A skin lesion imaged with a dermatoscope.
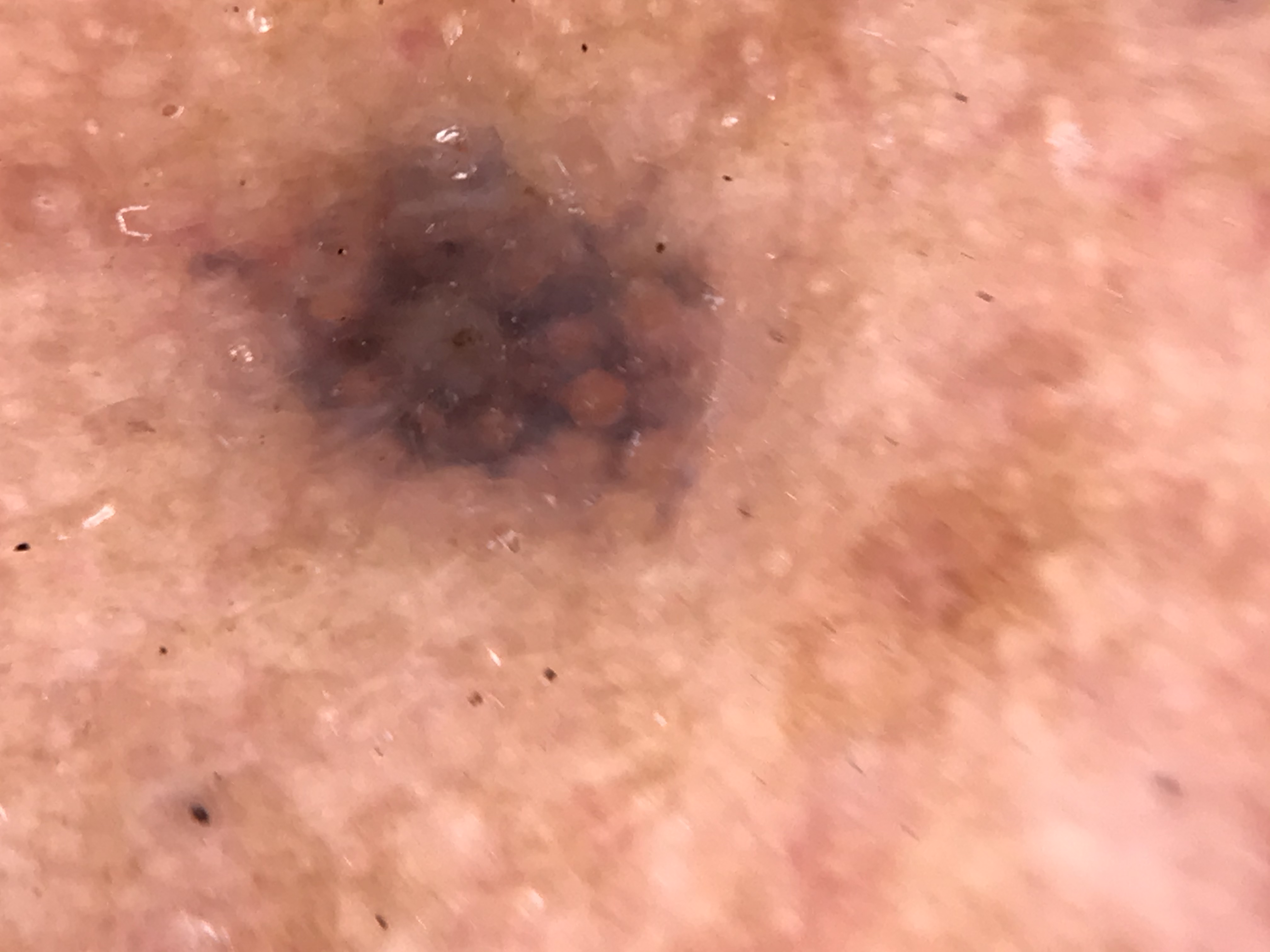assessment: Miescher nevus (expert consensus).